A dermatoscopic image of a skin lesion.
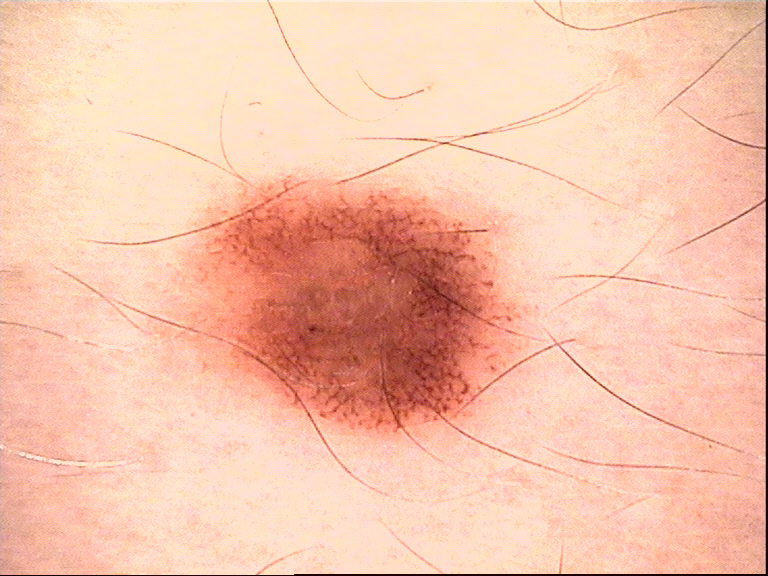Classified as a dysplastic junctional nevus.